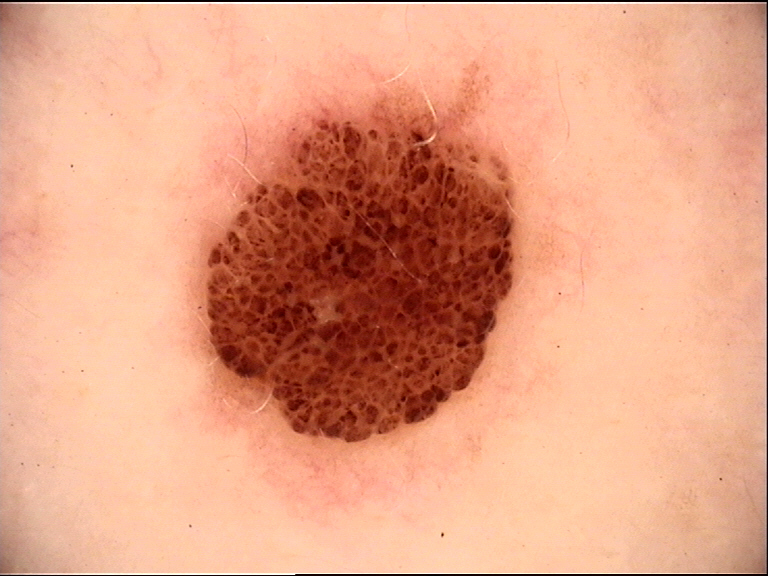Findings:
• image type · dermoscopy
• lesion type · banal
• assessment · compound nevus (expert consensus)